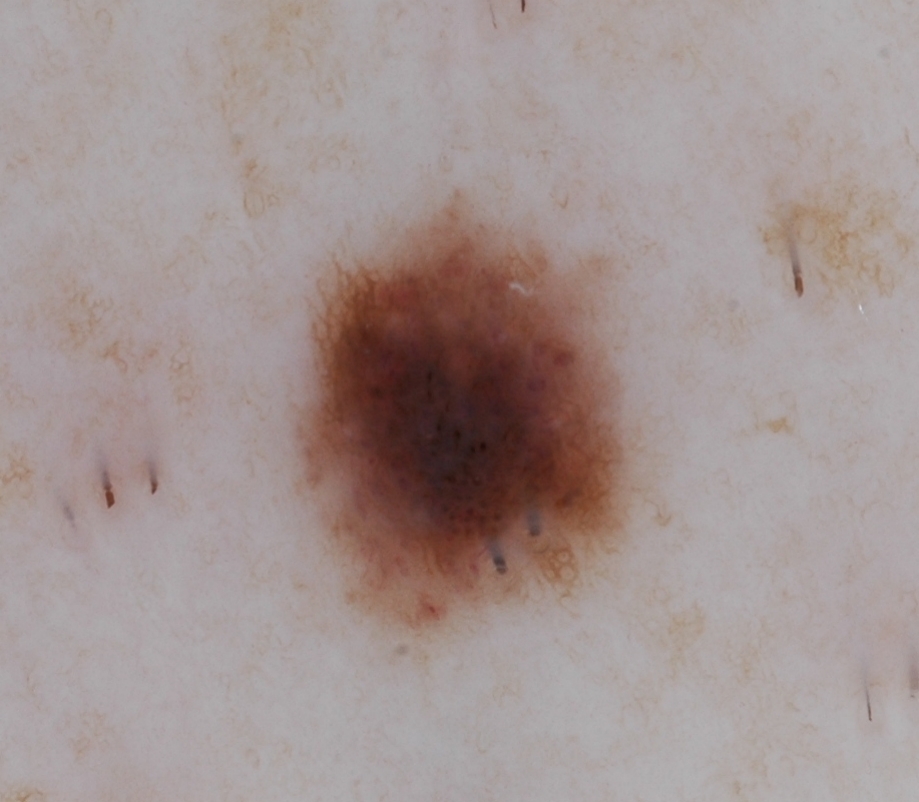Dermoscopy of a skin lesion. Dermoscopic assessment notes pigment network and globules, with no milia-like cysts, negative network, or streaks. The lesion occupies roughly 14% of the field. As (left, top, right, bottom), the lesion is bounded by box(292, 194, 629, 628). Clinically diagnosed as a melanocytic nevus, a benign skin lesion.